The chart notes no melanoma in first-degree relatives and no previous melanoma; FST II; a clinical photograph showing a skin lesion in context — 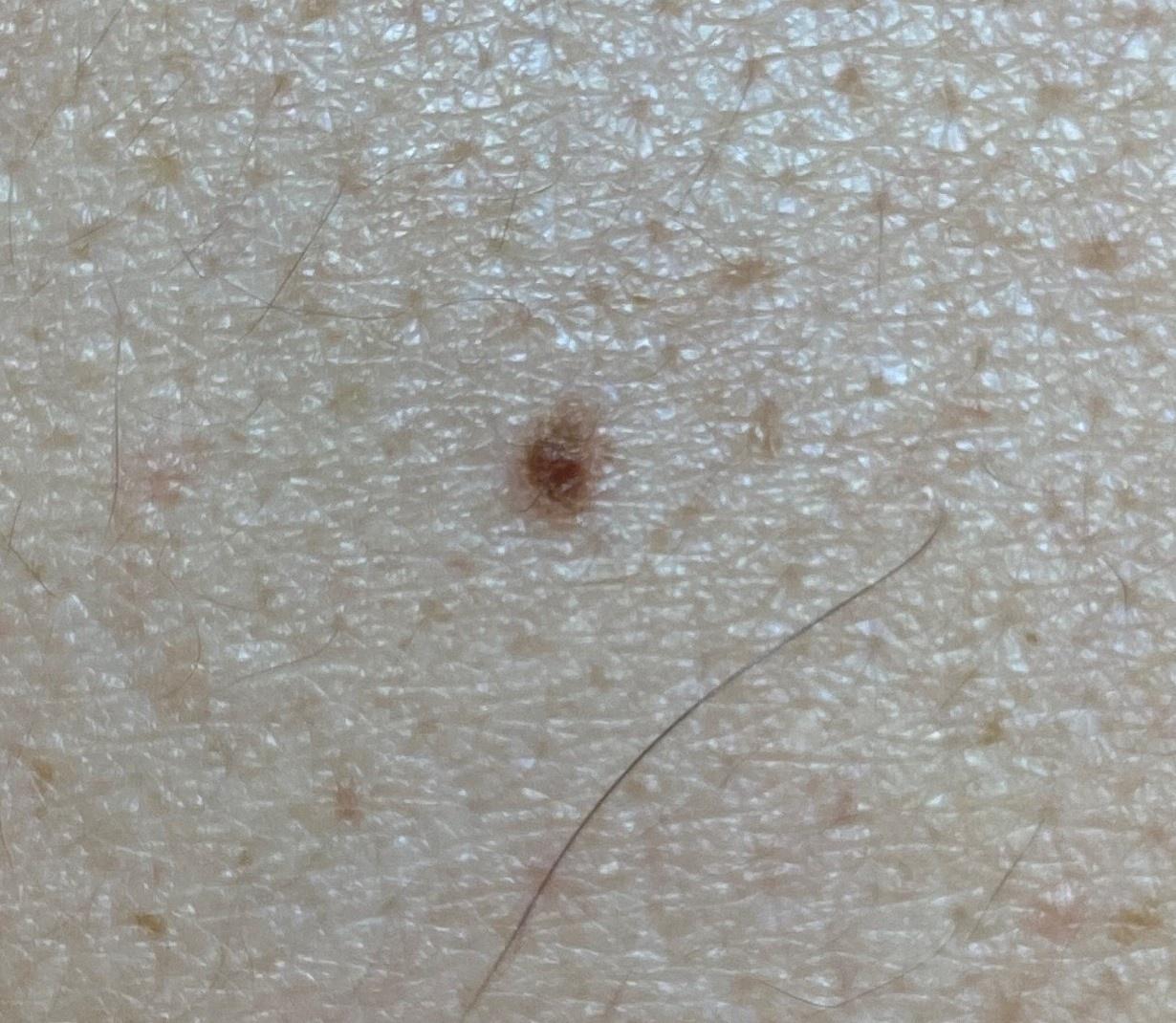diagnosis:
  name: Nevus
  malignancy: benign
  confirmation: histopathology
  lineage: melanocytic